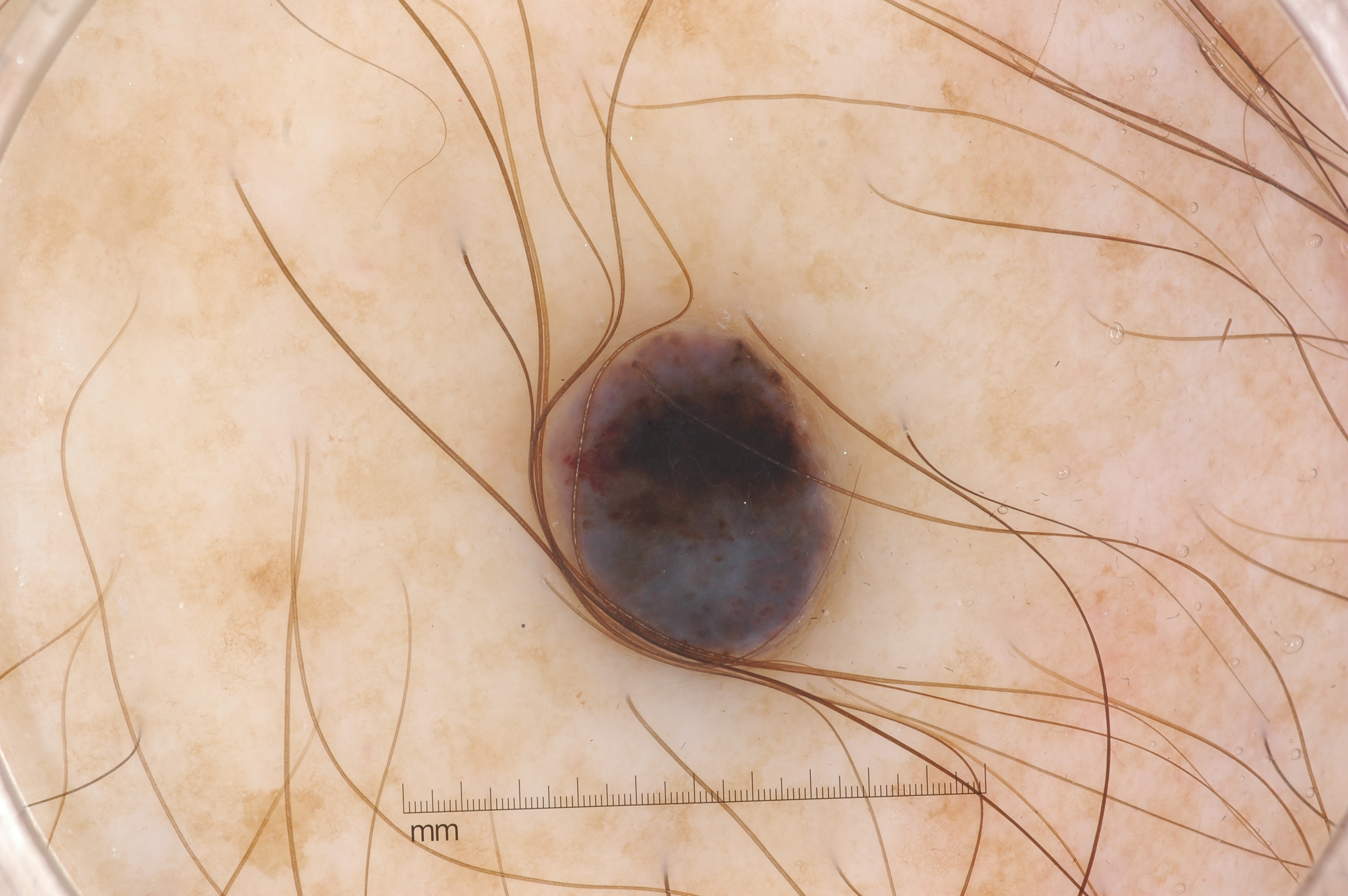  image:
    modality: dermoscopy
  dermoscopic_features:
    present:
      - milia-like cysts
    absent:
      - streaks
      - negative network
      - pigment network
  lesion_location:
    bbox_xyxy:
      - 537
      - 300
      - 853
      - 665
  diagnosis:
    name: melanoma
    malignancy: malignant
    lineage: melanocytic
    provenance: histopathology